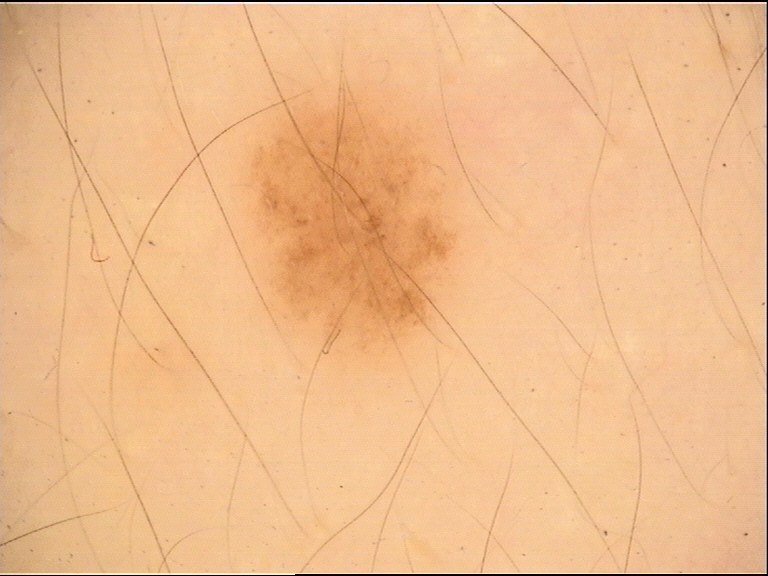Summary:
A dermoscopic photograph of a skin lesion.
Impression:
Classified as a dysplastic junctional nevus.